A male patient aged approximately 70, dermoscopy of a skin lesion:
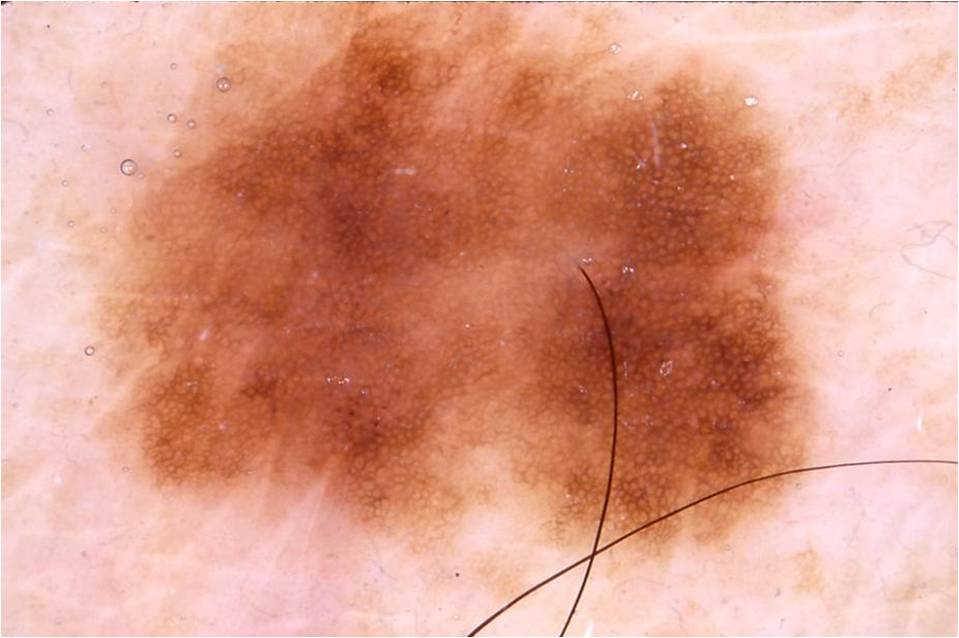Dermoscopic examination shows pigment network, globules, and milia-like cysts; no streaks or negative network. With coordinates (x1, y1, x2, y2), the lesion spans <bbox>61, 2, 830, 577</bbox>. The diagnostic assessment was a melanocytic nevus.